A dermoscopic photograph of a skin lesion.
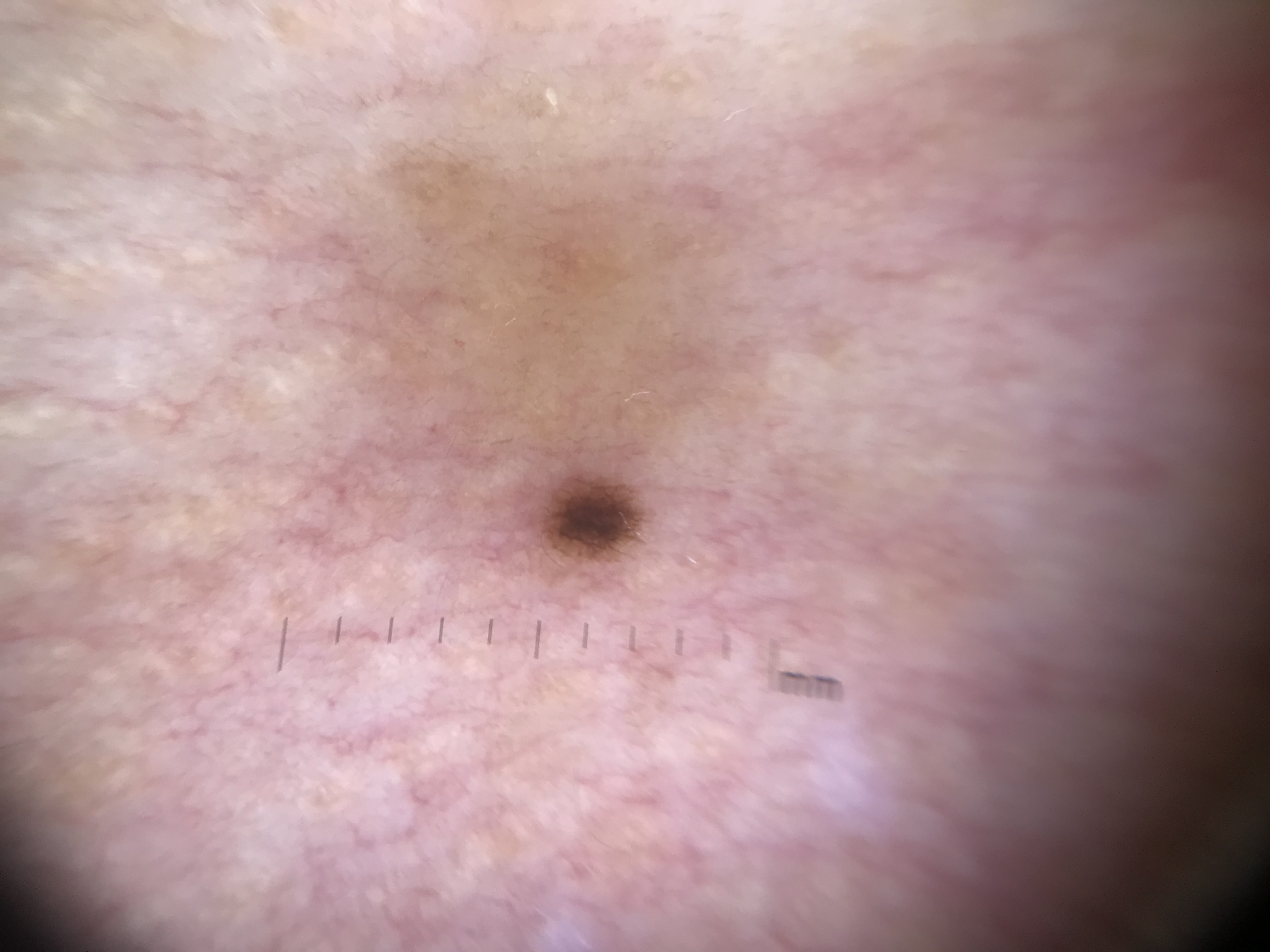Q: What is this lesion?
A: junctional nevus (expert consensus)